Located on the back of the hand. The photo was captured at a distance. The subject is 40–49, female.
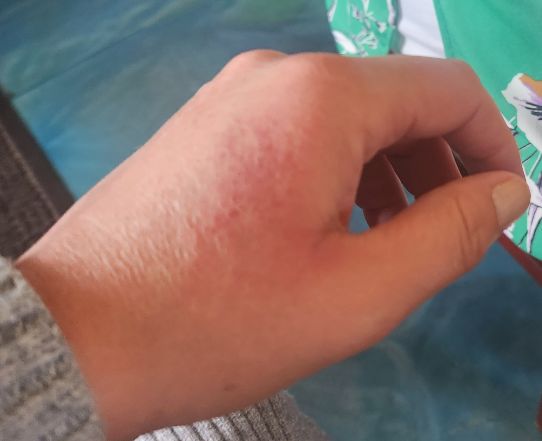Findings:
• assessment · most likely Eczema